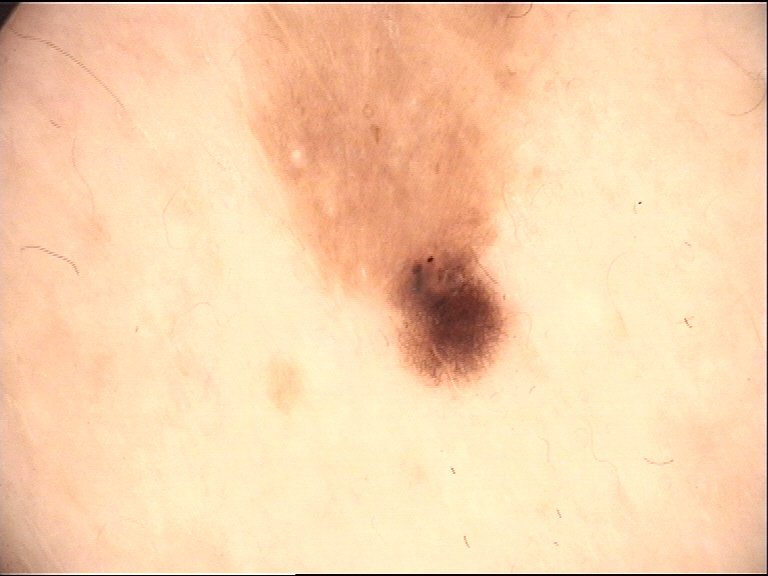Conclusion: Labeled as a dysplastic junctional nevus.